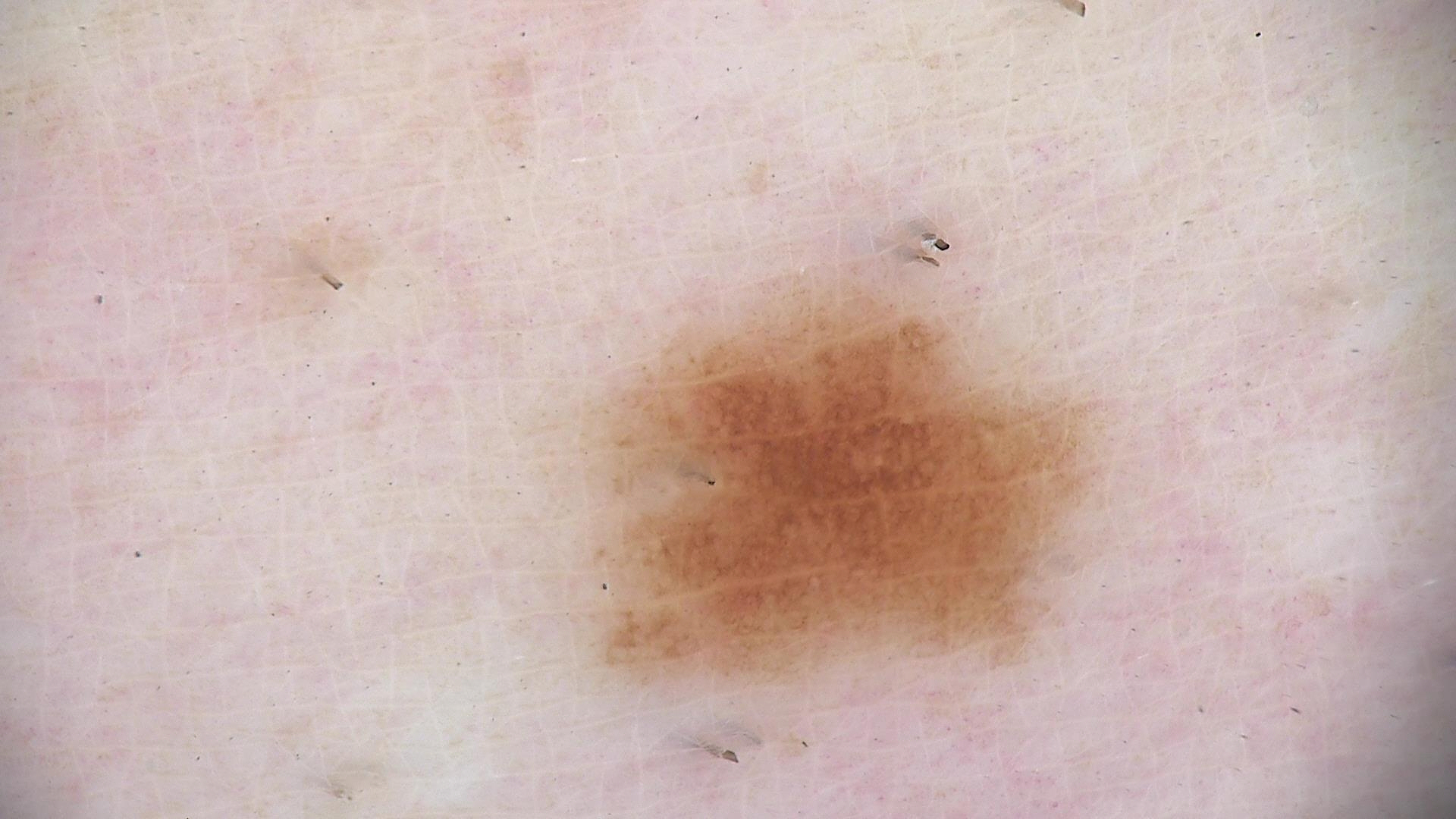diagnostic label=dysplastic junctional nevus (expert consensus).